A dermatoscopic image of a skin lesion.
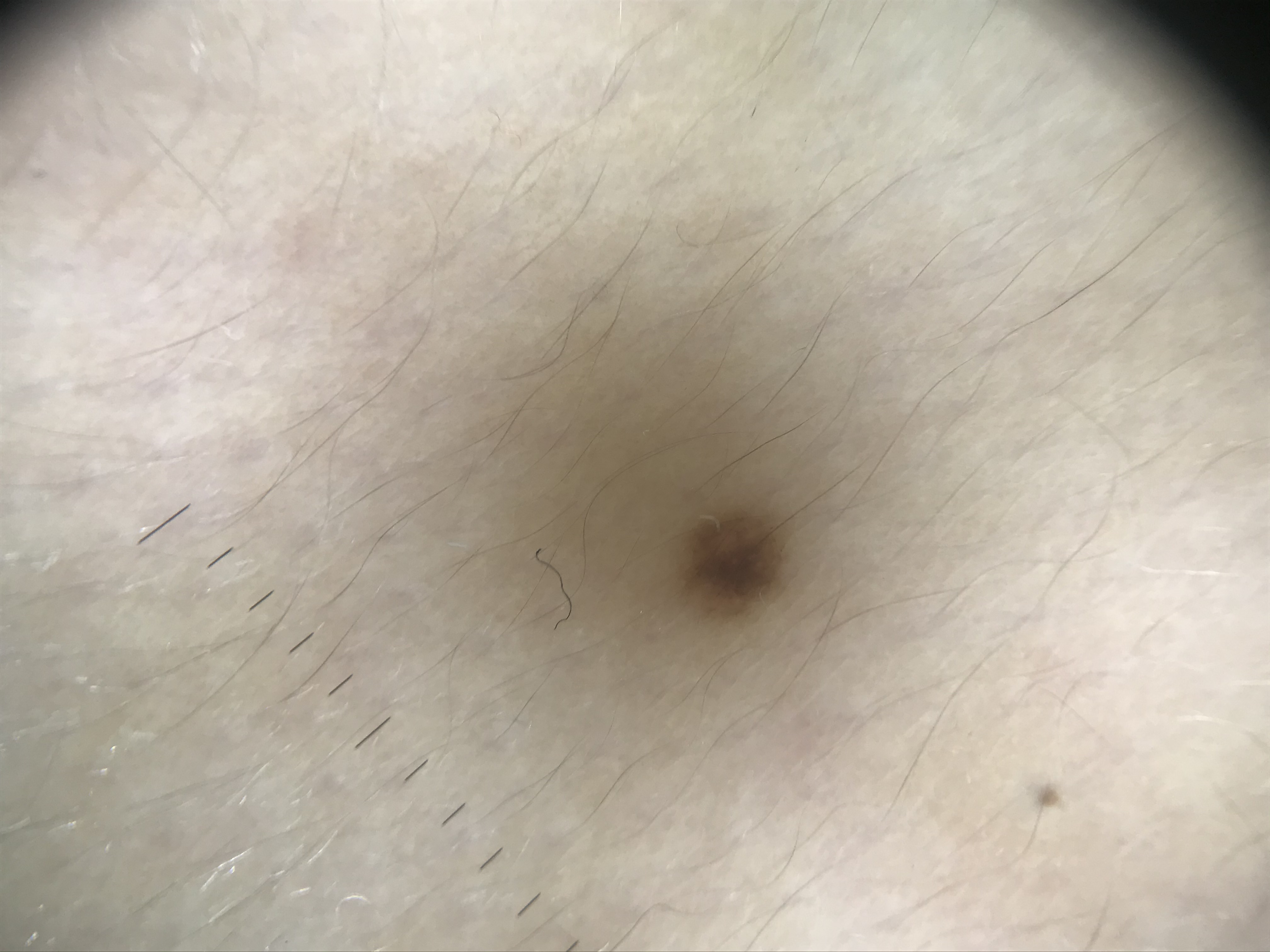Impression: Consistent with a banal lesion — a junctional nevus.